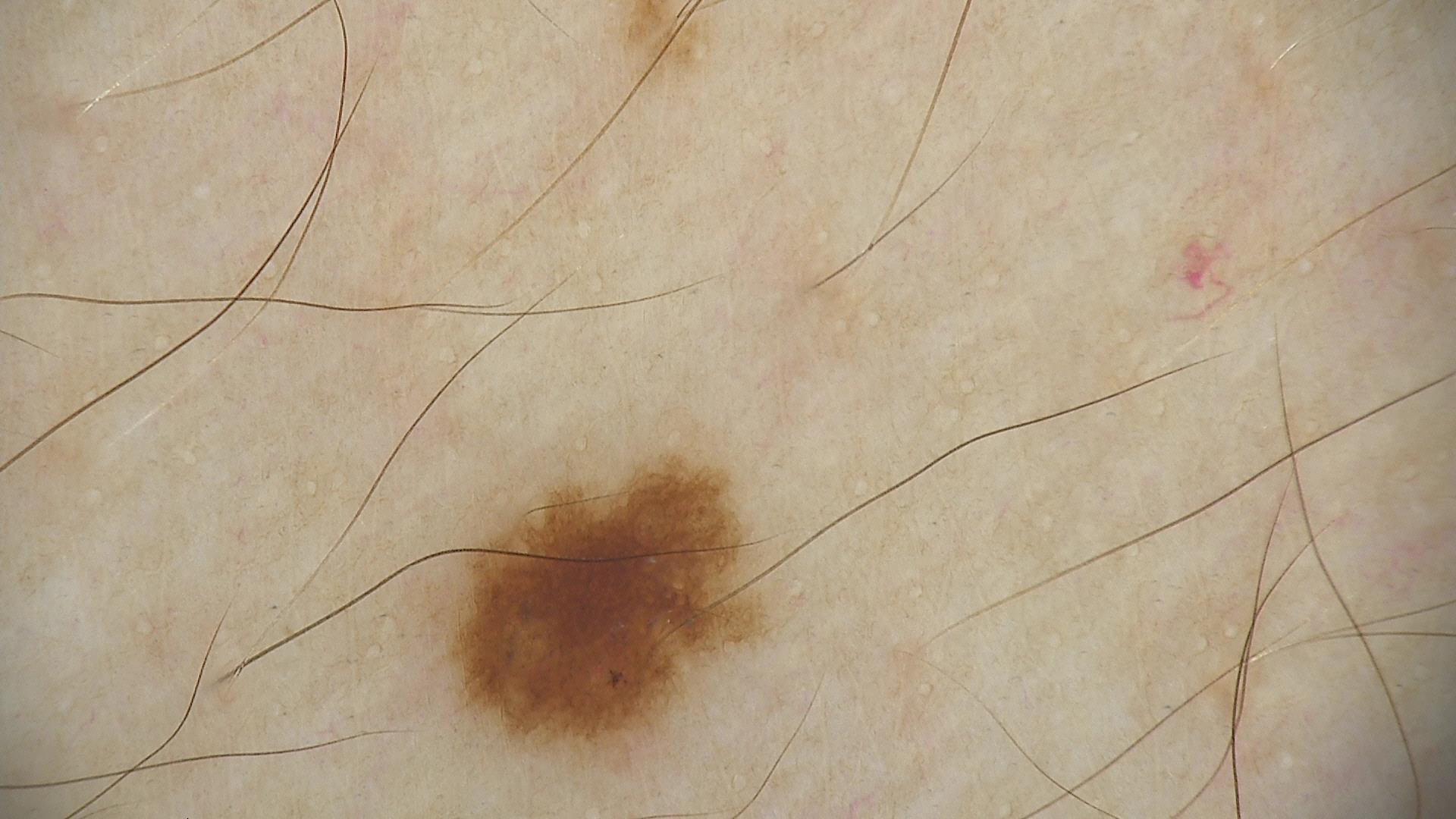| key | value |
|---|---|
| assessment | dysplastic junctional nevus (expert consensus) |